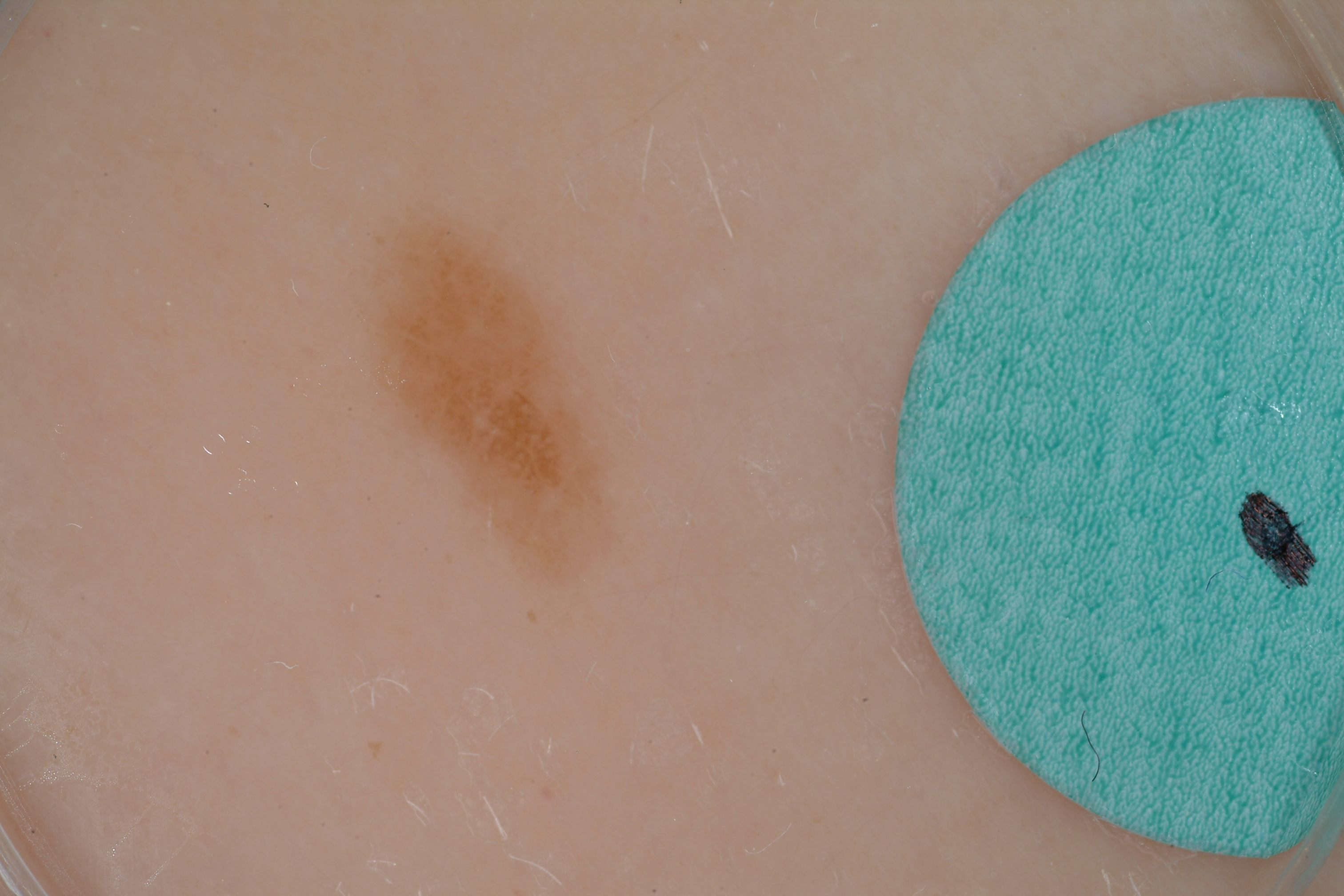Summary:
A dermoscopy image of a single skin lesion. The lesion is located at x1=350 y1=163 x2=619 y2=593.
Conclusion:
Expert review diagnosed this as a benign lesion.